Dermoscopy of a skin lesion: 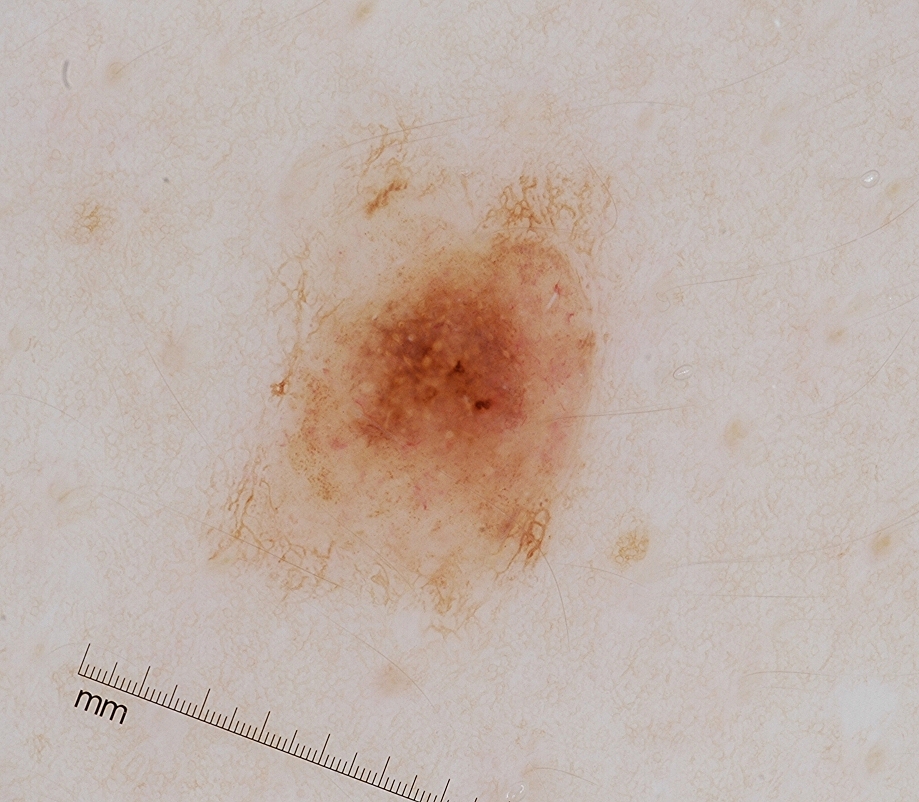Summary: Dermoscopic assessment notes globules. The visible lesion spans left=200, top=121, right=610, bottom=632. Conclusion: The clinical diagnosis was a melanocytic nevus, a benign lesion.